The front of the torso is involved; texture is reported as flat; a close-up photograph; male subject, age 18–29; reported duration is about one day; no associated lesion symptoms were reported — 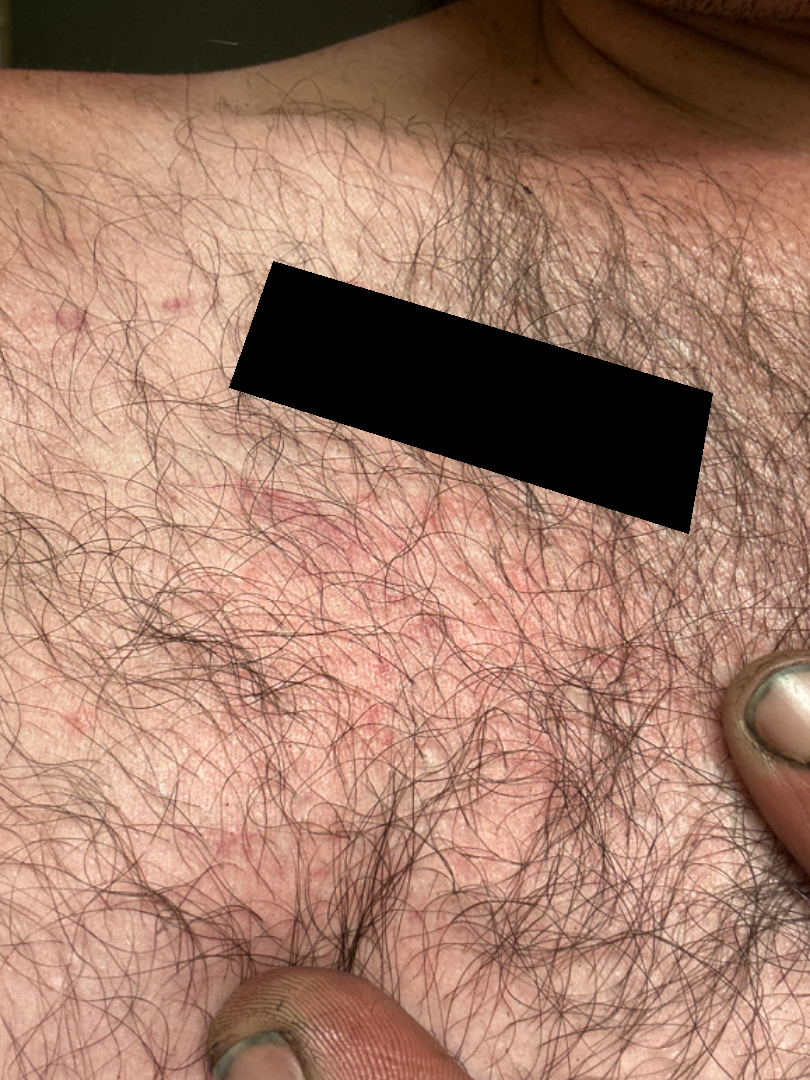| feature | finding |
|---|---|
| assessment | not assessable |